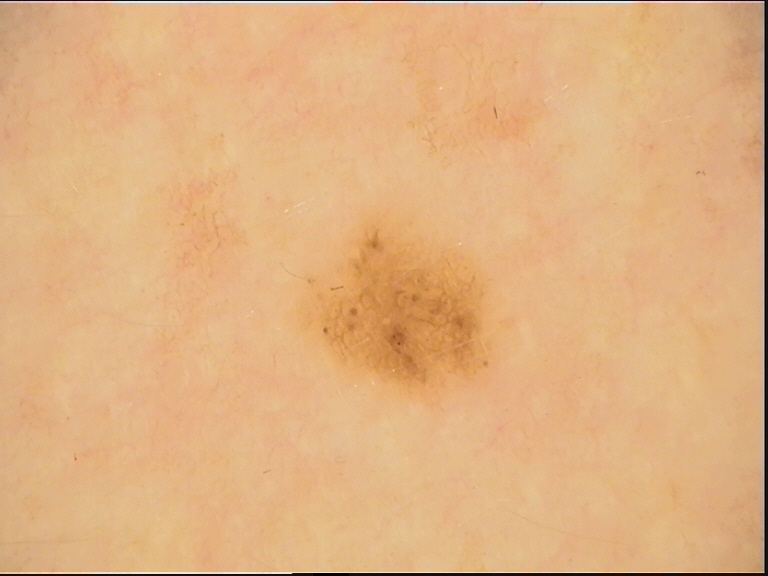A dermoscopic close-up of a skin lesion. Classified as a benign lesion — a dysplastic junctional nevus.